A dermoscopic image of a skin lesion · the patient is skin type II — 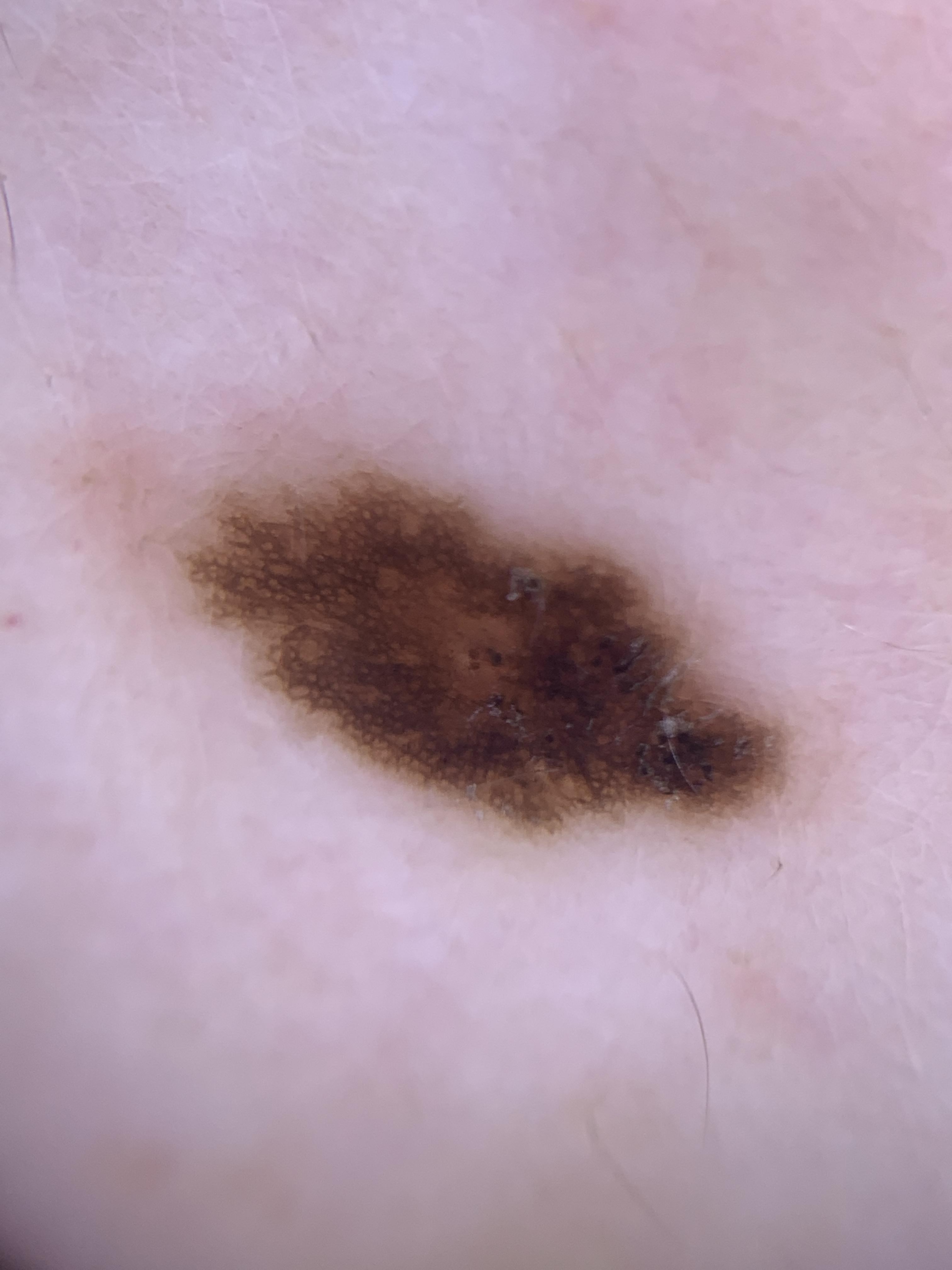Histopathologically confirmed as a benign, melanocytic lesion — a nevus.